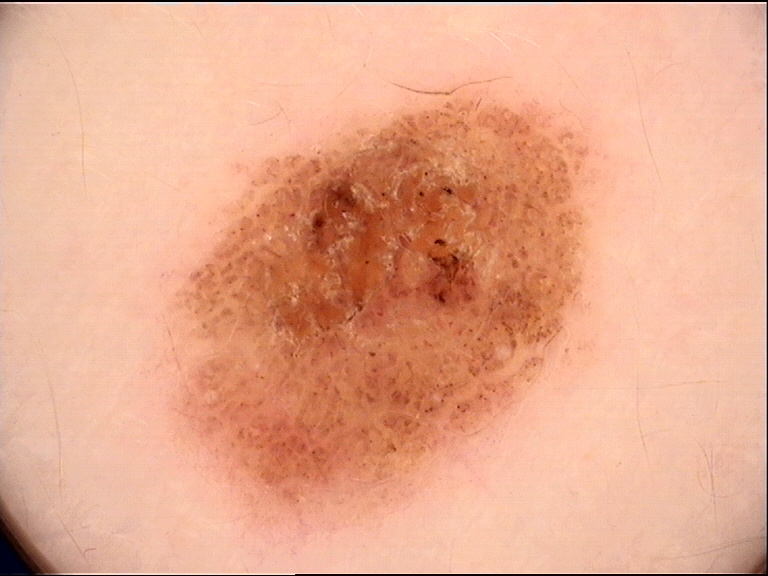modality = dermoscopy
diagnosis = compound nevus (expert consensus)